Skin tone: Fitzpatrick I, the photograph was taken at an angle, the lesion is associated with burning, the lesion involves the arm, the patient described the issue as a rash, the patient indicates the lesion is rough or flaky, no associated systemic symptoms reported — 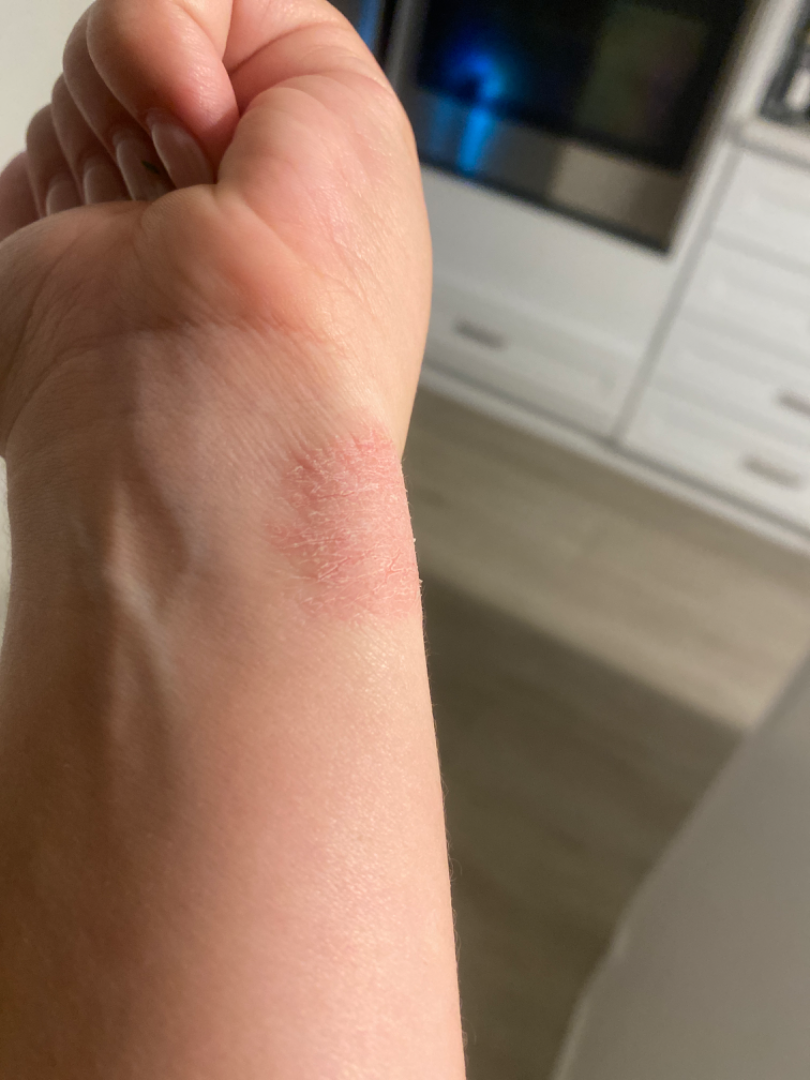  differential: Eczema